A clinical close-up photograph of a skin lesion. History notes prior malignancy (patient or family). A female patient age 61: 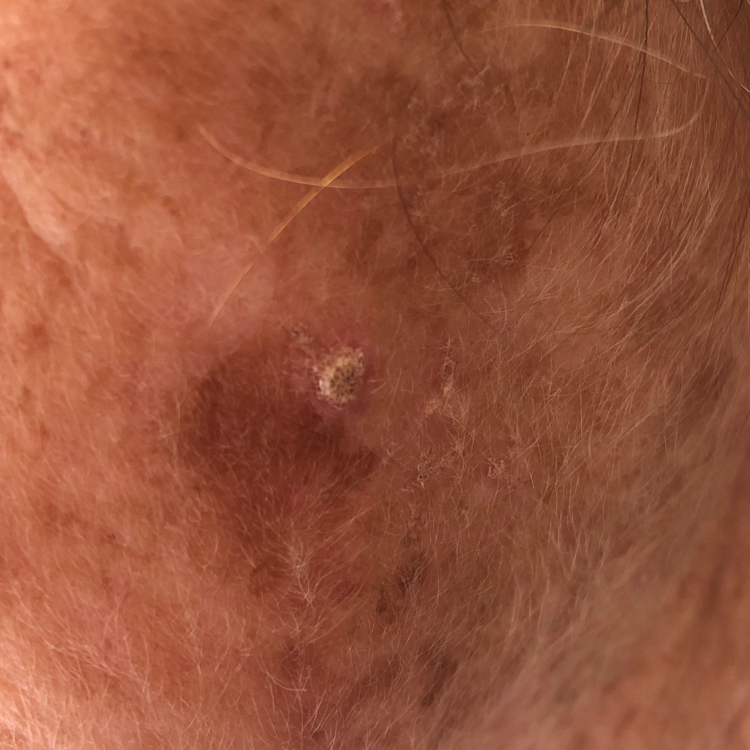anatomic site: the face
patient-reported symptoms: growth, change in appearance, elevation
pathology: actinic keratosis (biopsy-proven)